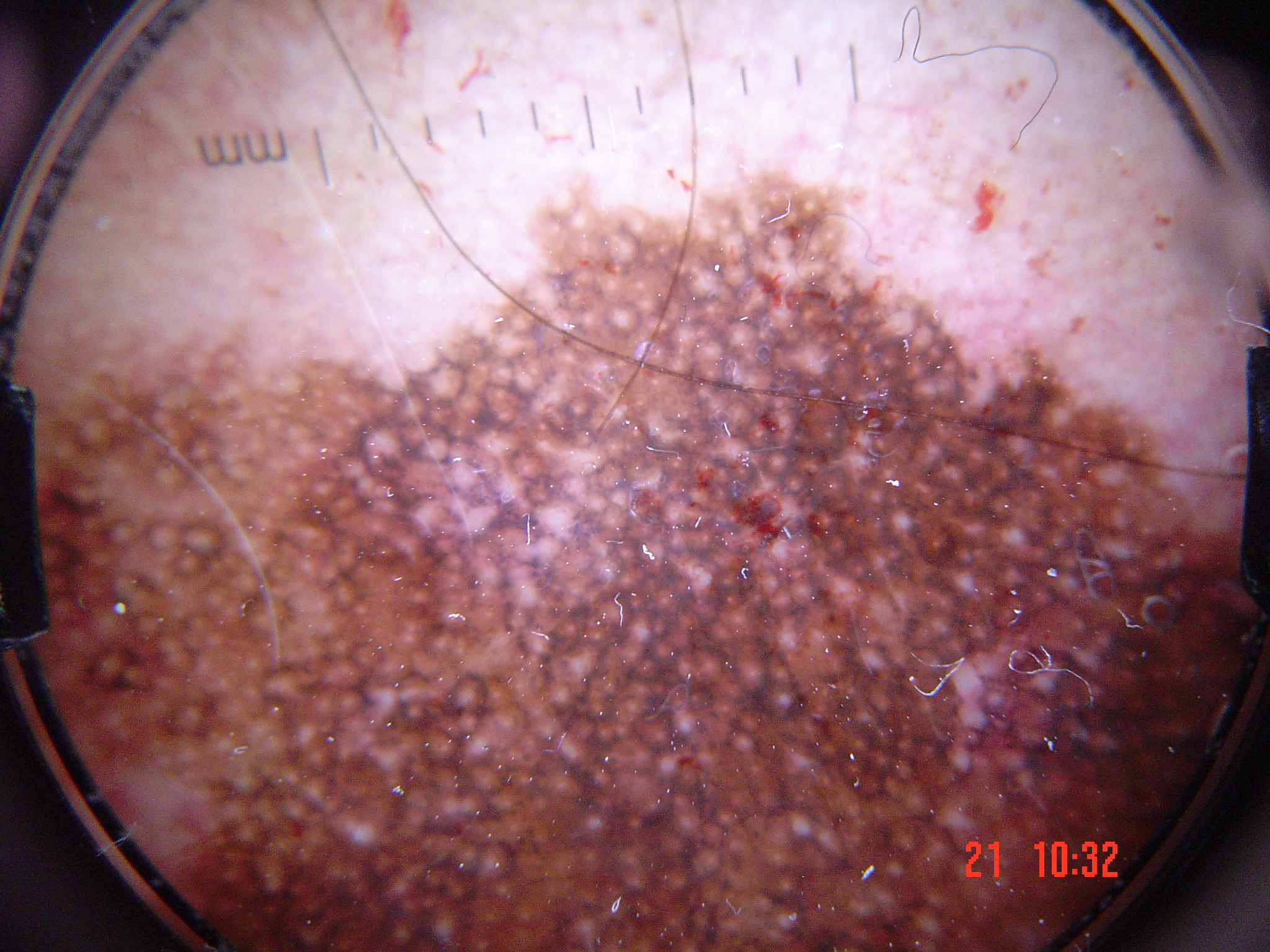image: dermatoscopy, diagnosis: lentigo maligna (biopsy-proven).